A female patient age 75.
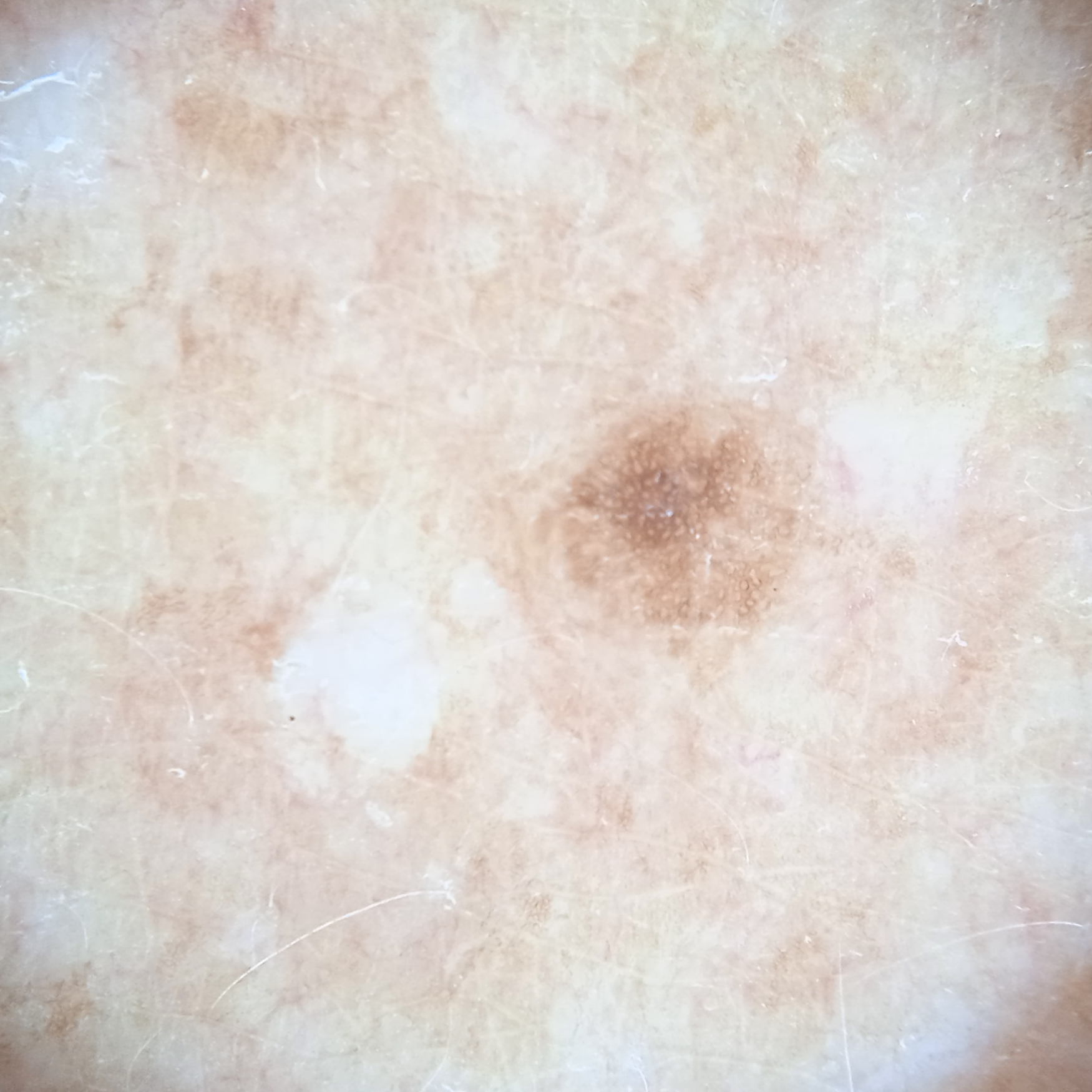location — the back
diagnosis — melanocytic nevus (dermatologist consensus)